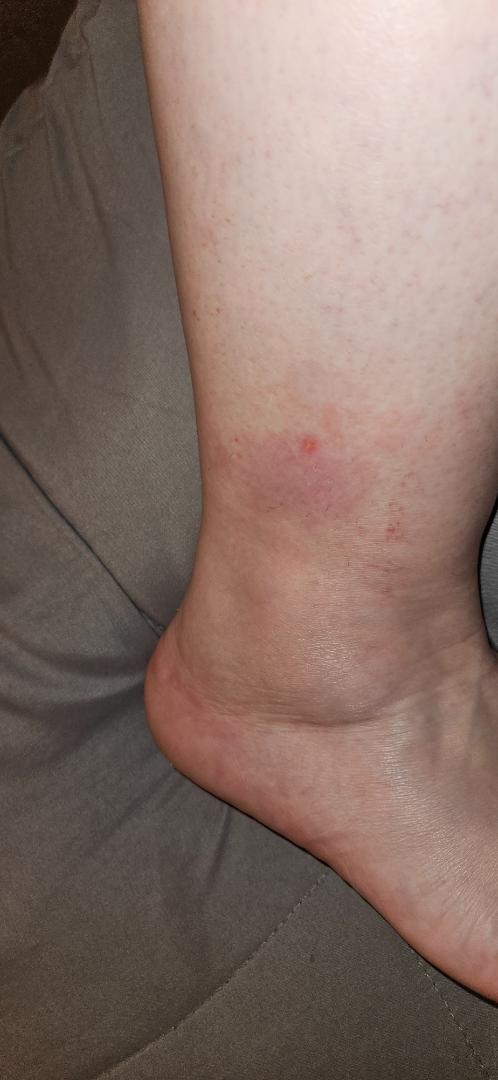The photo was captured at an angle. On dermatologist assessment of the image, favoring Stasis Dermatitis; also raised was Livedoid vasculopathy.